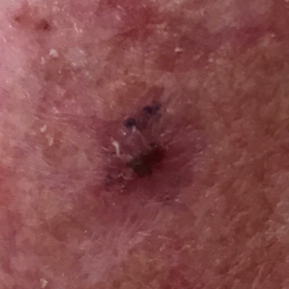The patient was assessed as Fitzpatrick skin type II.
A clinical close-up photograph of a skin lesion.
A female patient in their 60s.
The lesion is located on the face.
The lesion measures approximately 6 × 5 mm.
The patient describes that the lesion itches.
Confirmed on histopathology as a lesion with uncertain malignant potential — an actinic keratosis.